A dermoscopic photograph of a skin lesion: 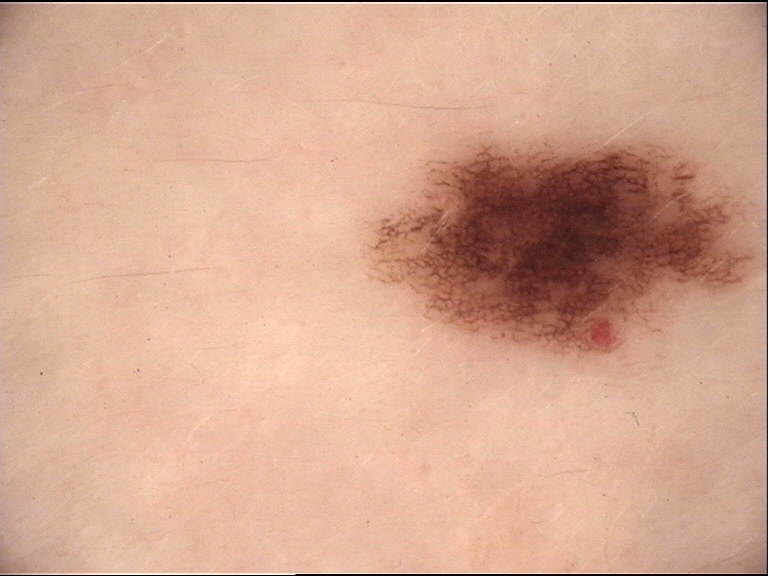Labeled as a dysplastic junctional nevus.